The subject is a female aged 30–39, the lesion involves the head or neck, an image taken at an angle — 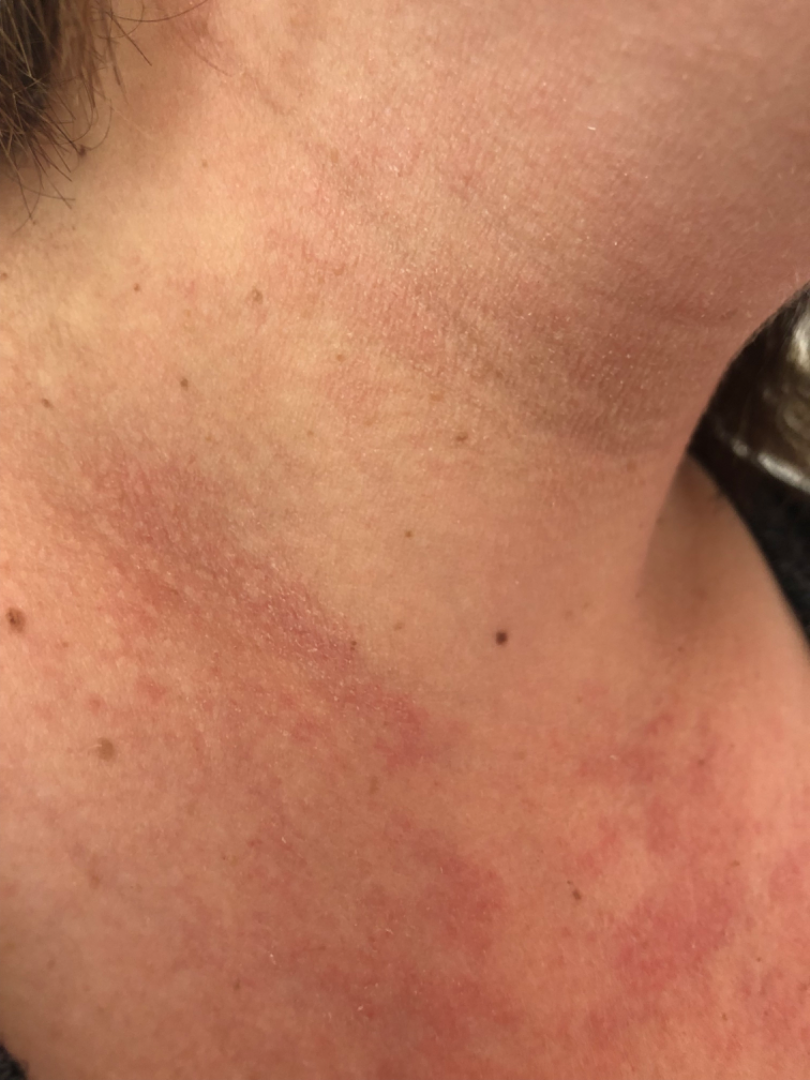{"differential": {"tied_lead": ["Allergic Contact Dermatitis", "Irritant Contact Dermatitis"]}}